A female subject aged 60 · the patient describes having few moles overall · collected as part of a research study, without a referral diagnosis · a dermoscopy image of a skin lesion · the patient reports a personal history of cancer and a personal history of skin cancer · the patient says their skin tans without first burning:
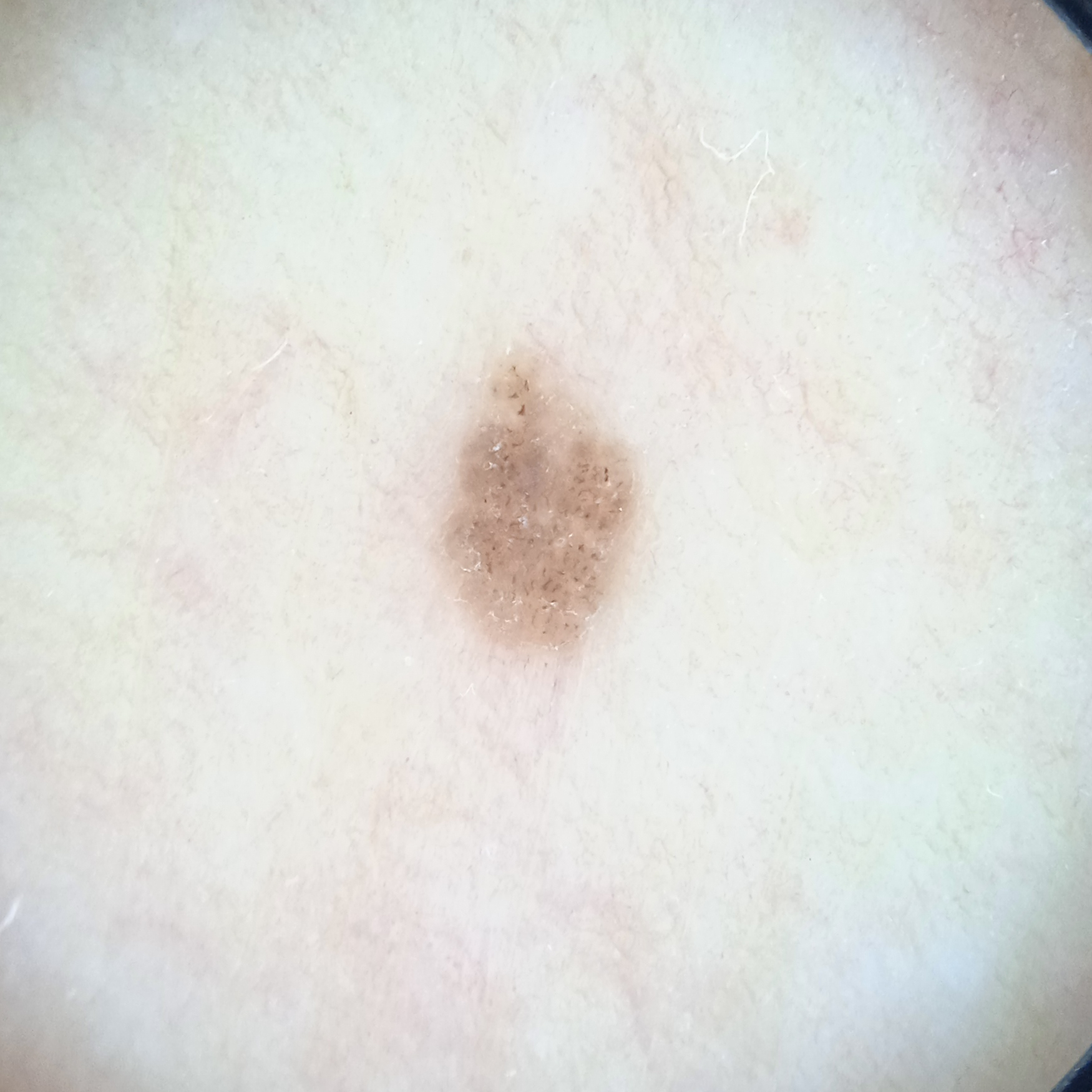The lesion is located on the torso. The lesion is about 3.4 mm across. The lesion was assessed as a melanocytic nevus.